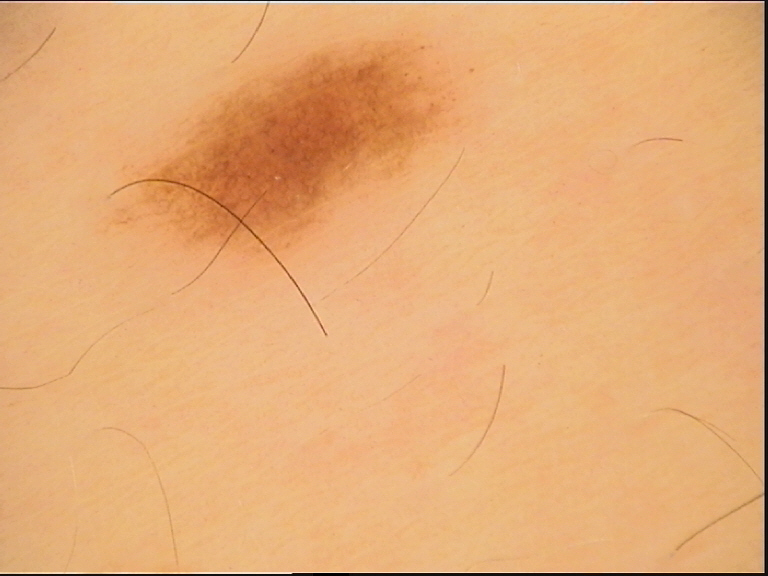The diagnosis was a dysplastic junctional nevus.